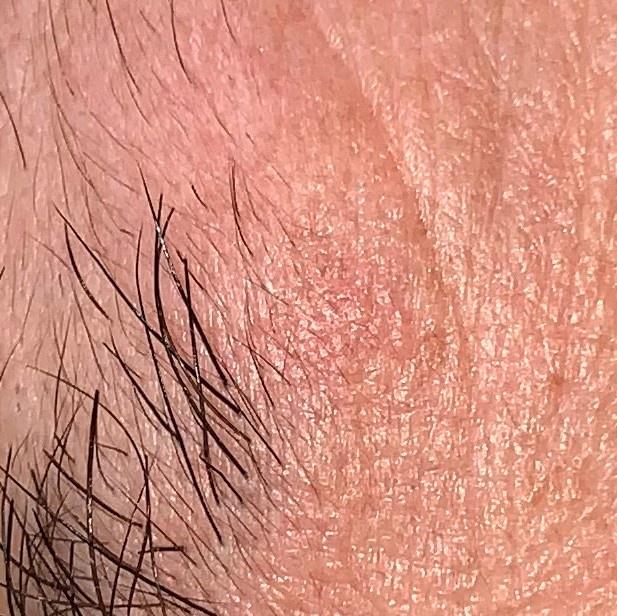| feature | finding |
|---|---|
| subject | male, aged 63 to 67 |
| modality | clinical photograph |
| anatomic site | the head or neck |
| diagnosis | Solar or actinic keratosis (clinical impression) |